The arm is involved; an image taken at a distance.
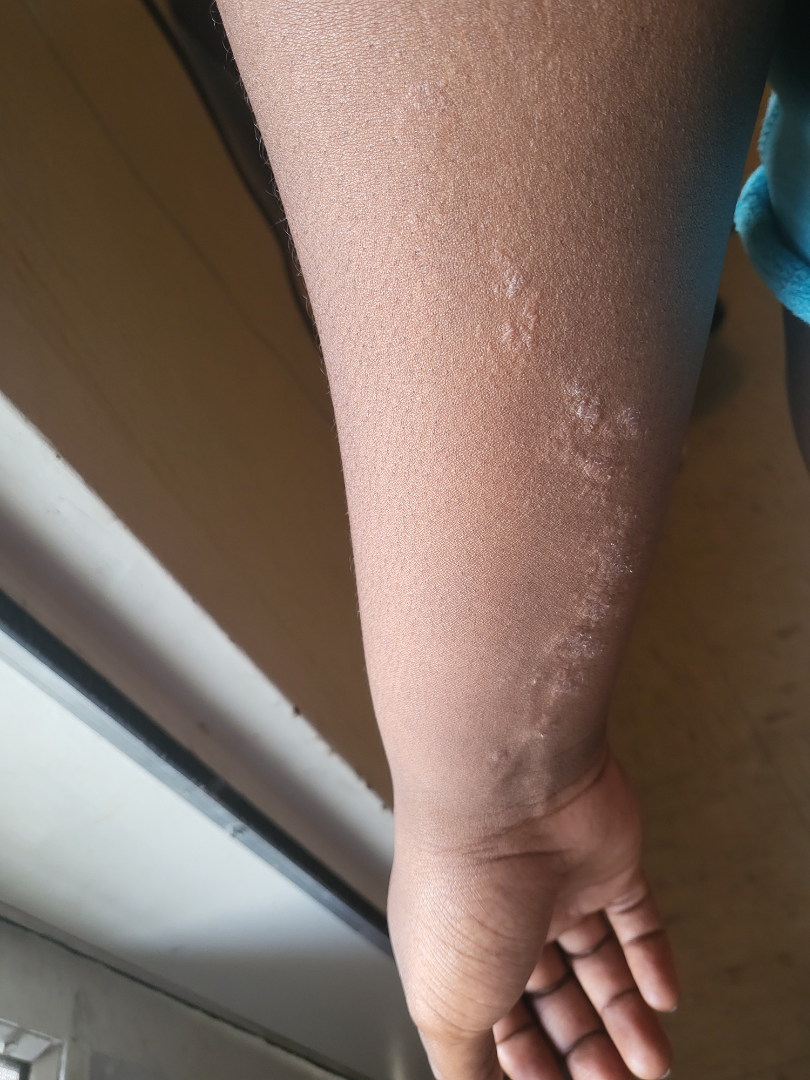{"differential": {"leading": ["Lichen striatus"]}}